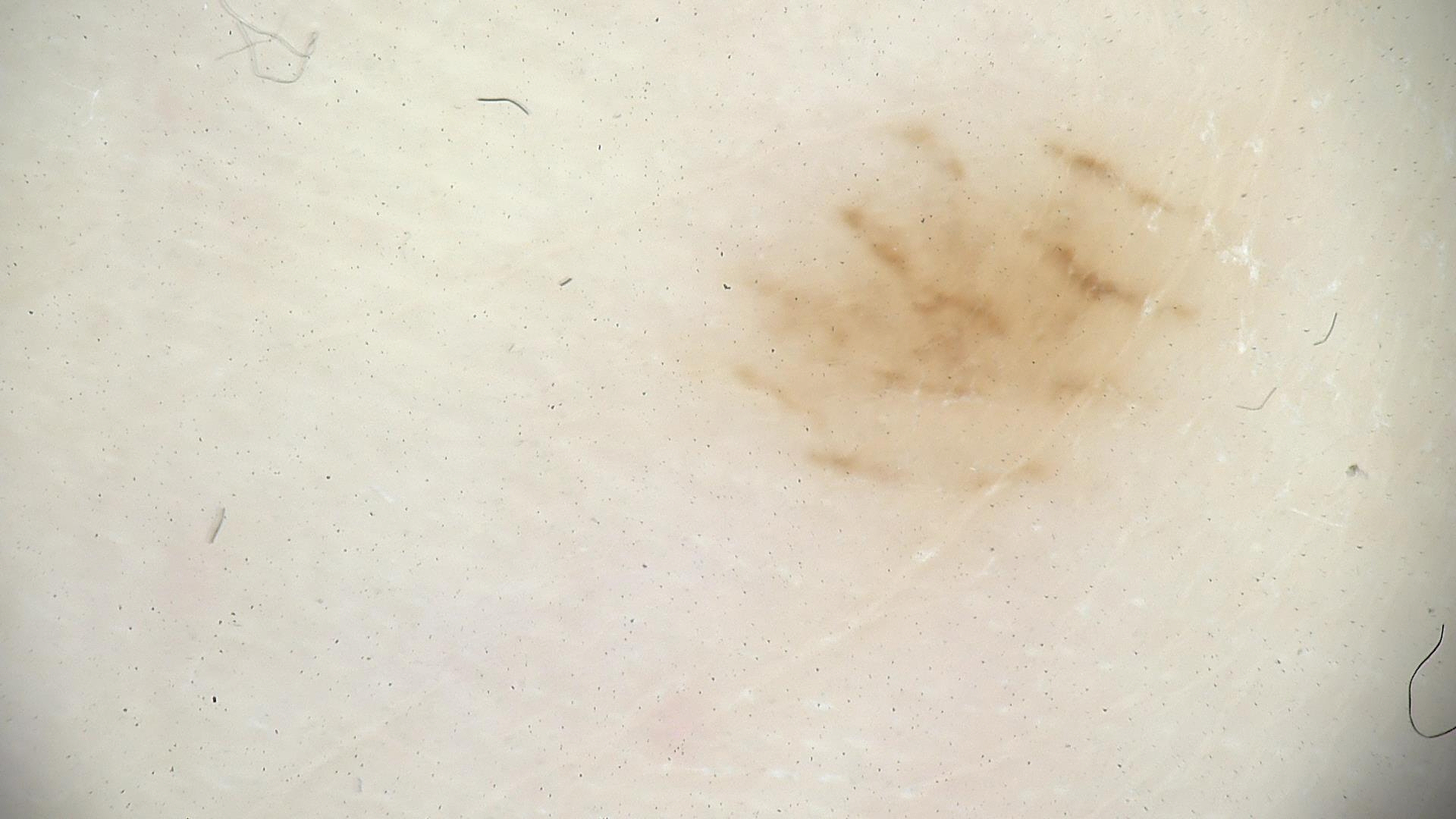A dermoscopic photograph of a skin lesion. Diagnosed as an acral dysplastic junctional nevus.